The chart notes prior malignancy (patient or family) · a female subject in their 60s · recorded as Fitzpatrick skin type II:
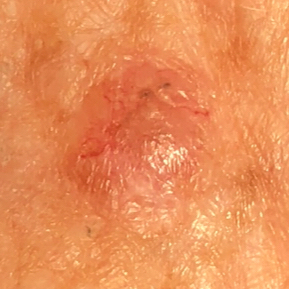Findings:
The lesion is located on the chest.
Conclusion:
On biopsy, the diagnosis was a skin cancer — a basal cell carcinoma.